A dermatoscopic image of a skin lesion.
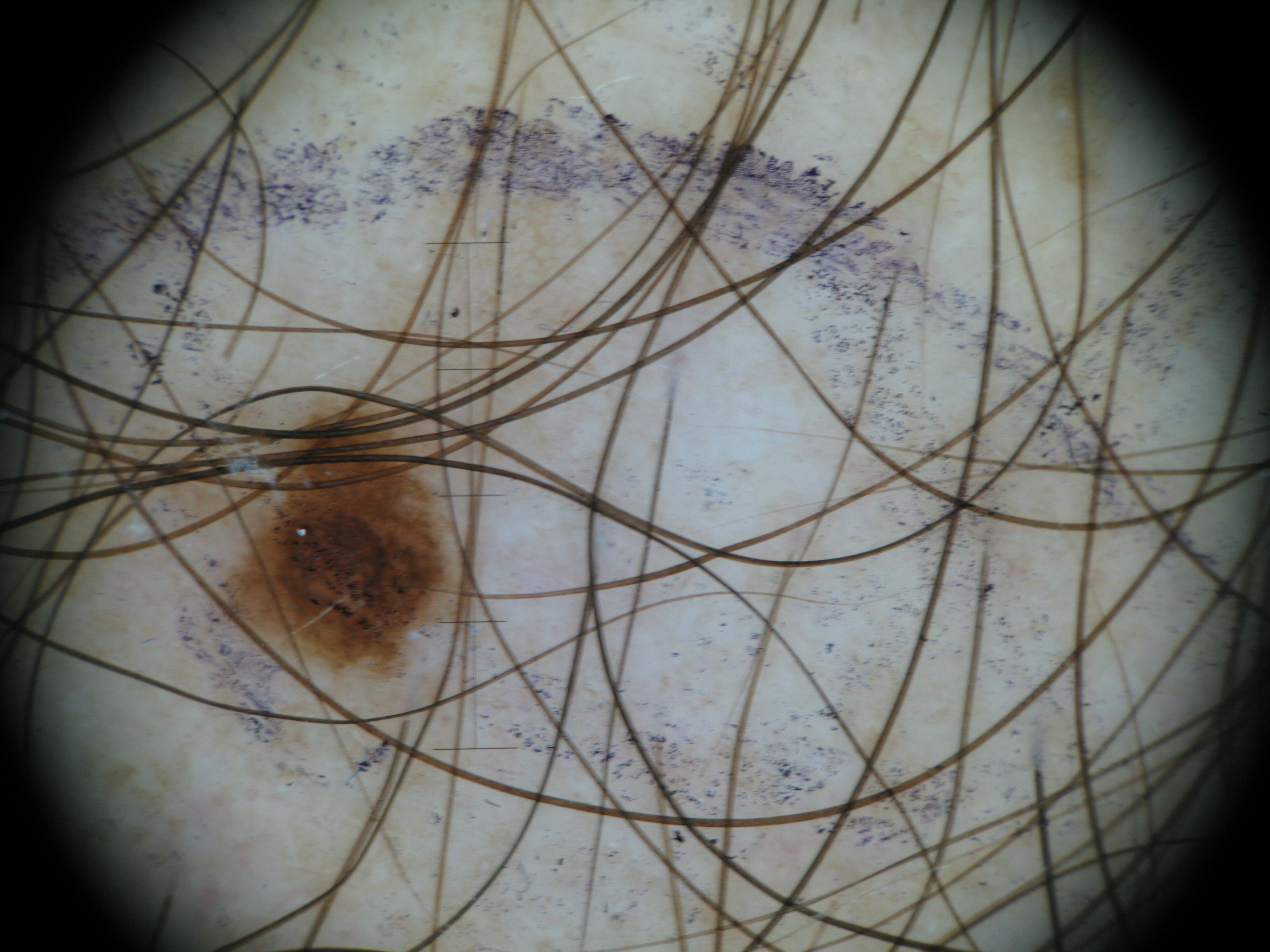diagnostic label: dysplastic junctional nevus (expert consensus).